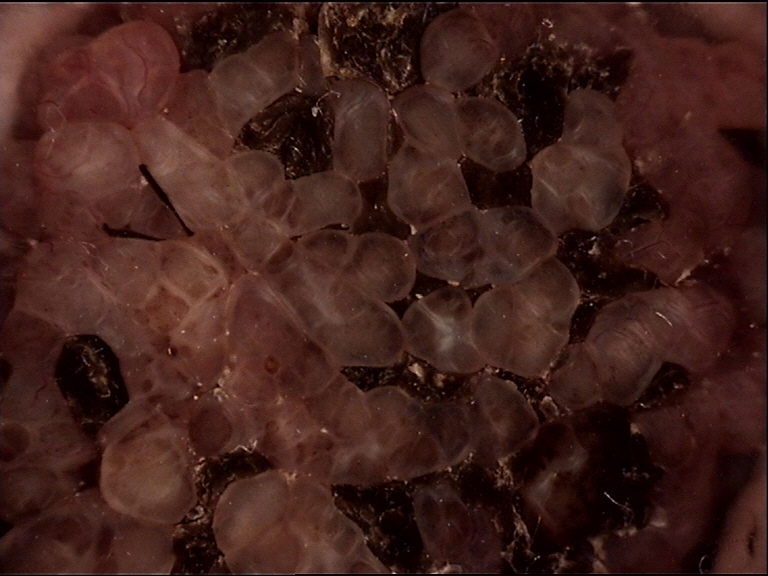– diagnosis — congenital compound nevus (expert consensus)